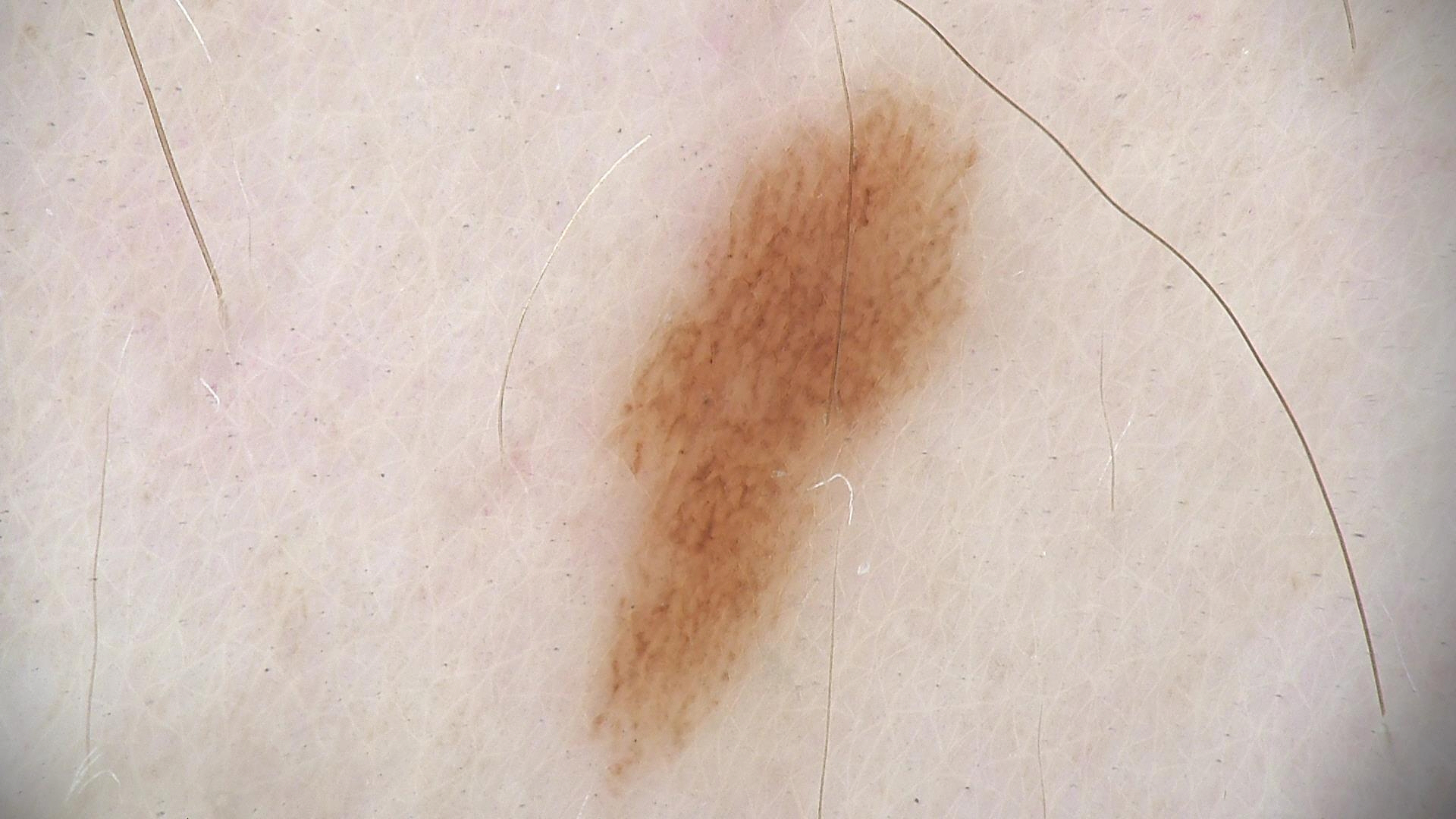Labeled as a dysplastic junctional nevus.